Self-categorized by the patient as a rash · the condition has been present for less than one week · texture is reported as raised or bumpy · the patient is a female aged 40–49 · a close-up photograph · the patient reported no systemic symptoms · located on the back of the hand, arm and front of the torso: 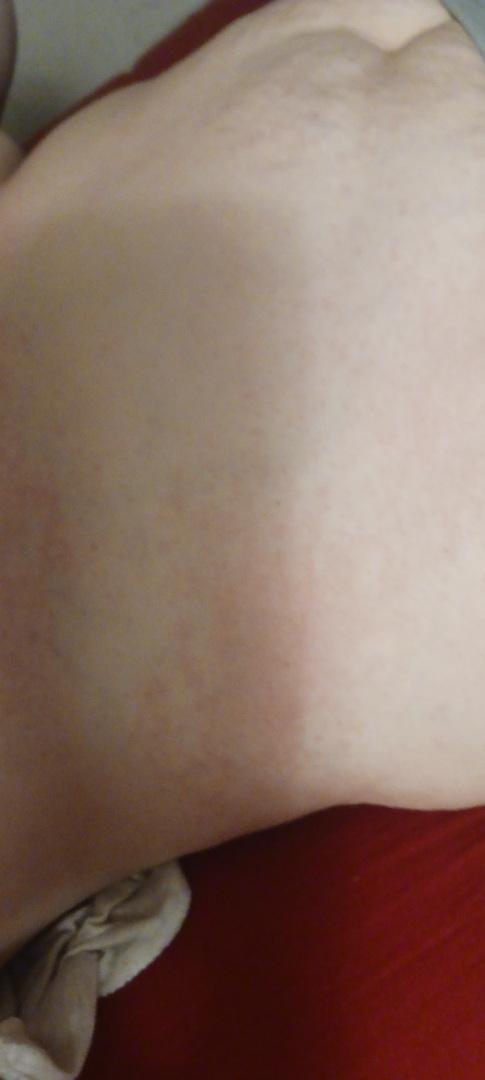Case summary:
- dermatologist impression — in keeping with Contact dermatitis